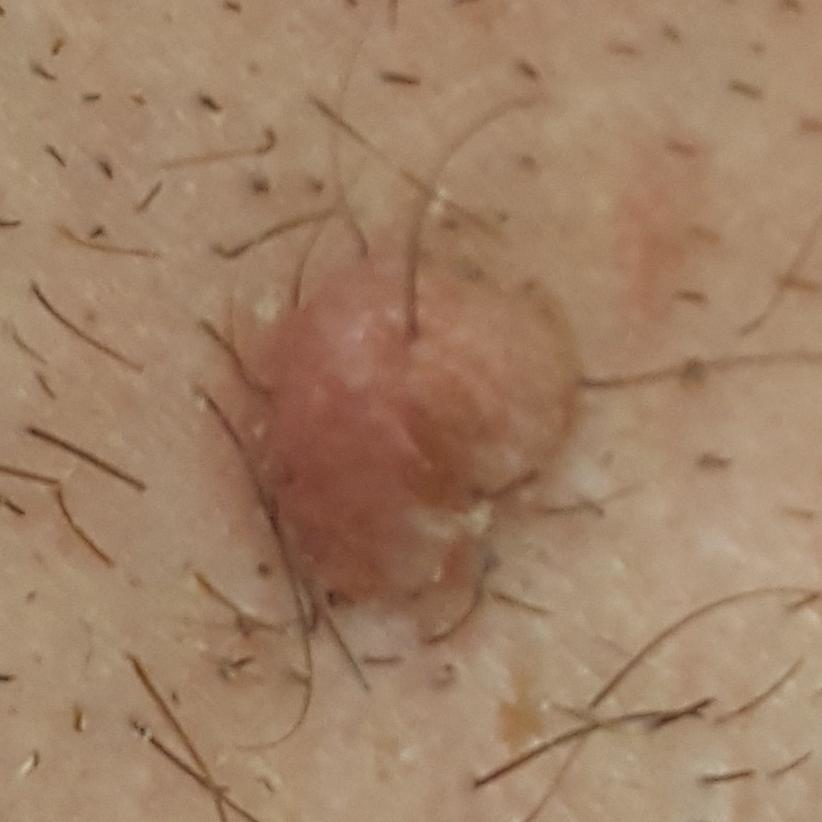Impression: Consistent with a nevus.